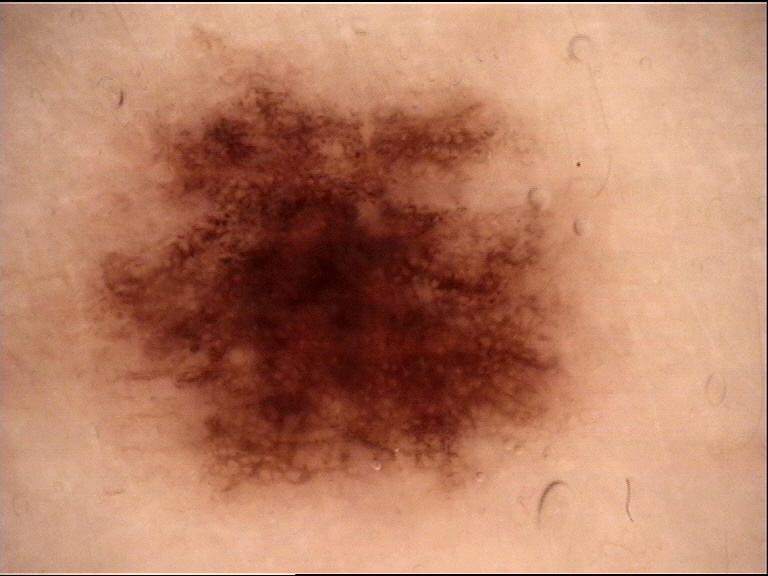The diagnostic label was a dysplastic junctional nevus.